The patient is 40–49, female. The photograph was taken at an angle. The lesion involves the palm, head or neck and arm.
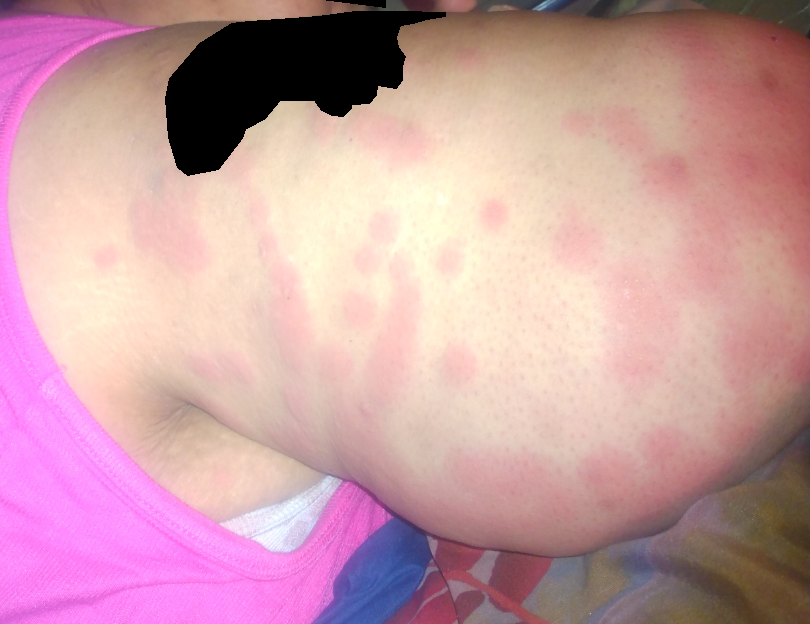On remote review of the image: Urticaria (most likely); Leukocytoclastic Vasculitis (possible); Insect Bite (lower probability).